The arm, head or neck, back of the torso, leg and back of the hand are involved · an image taken at a distance · the contributor is a female aged 30–39: 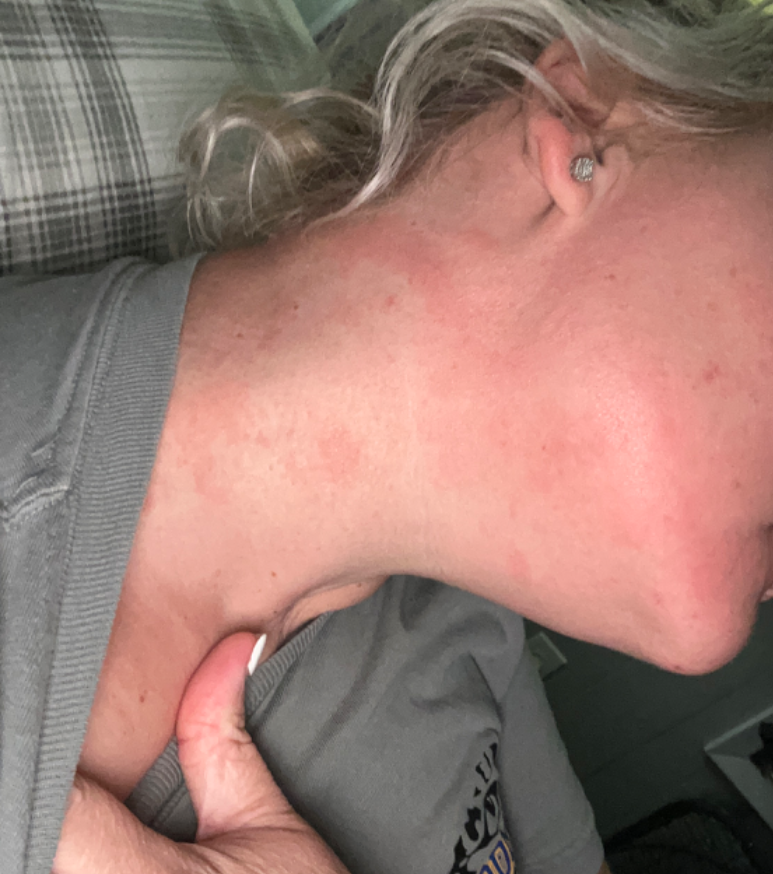Assessment: The differential includes Irritant Contact Dermatitis and Allergic Contact Dermatitis, with no clear leading consideration; also consider Eczema.